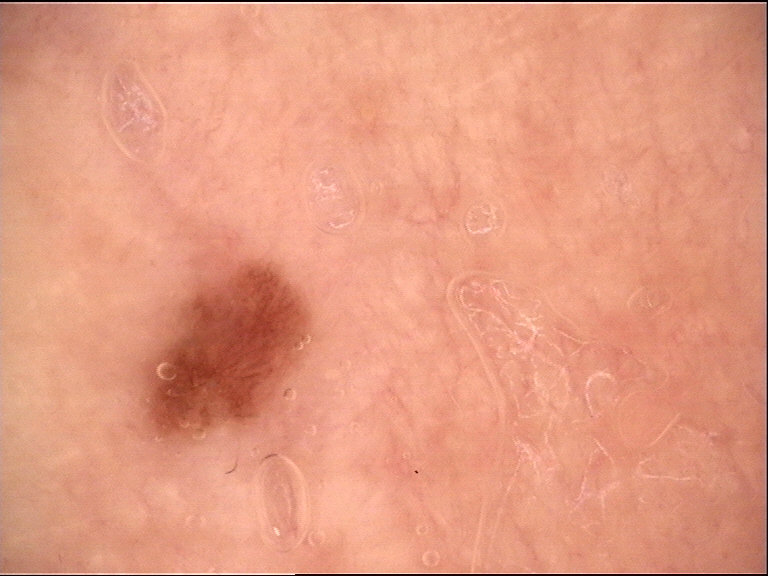Findings:
A dermoscopy image of a single skin lesion.
Impression:
Diagnosed as a dysplastic junctional nevus.